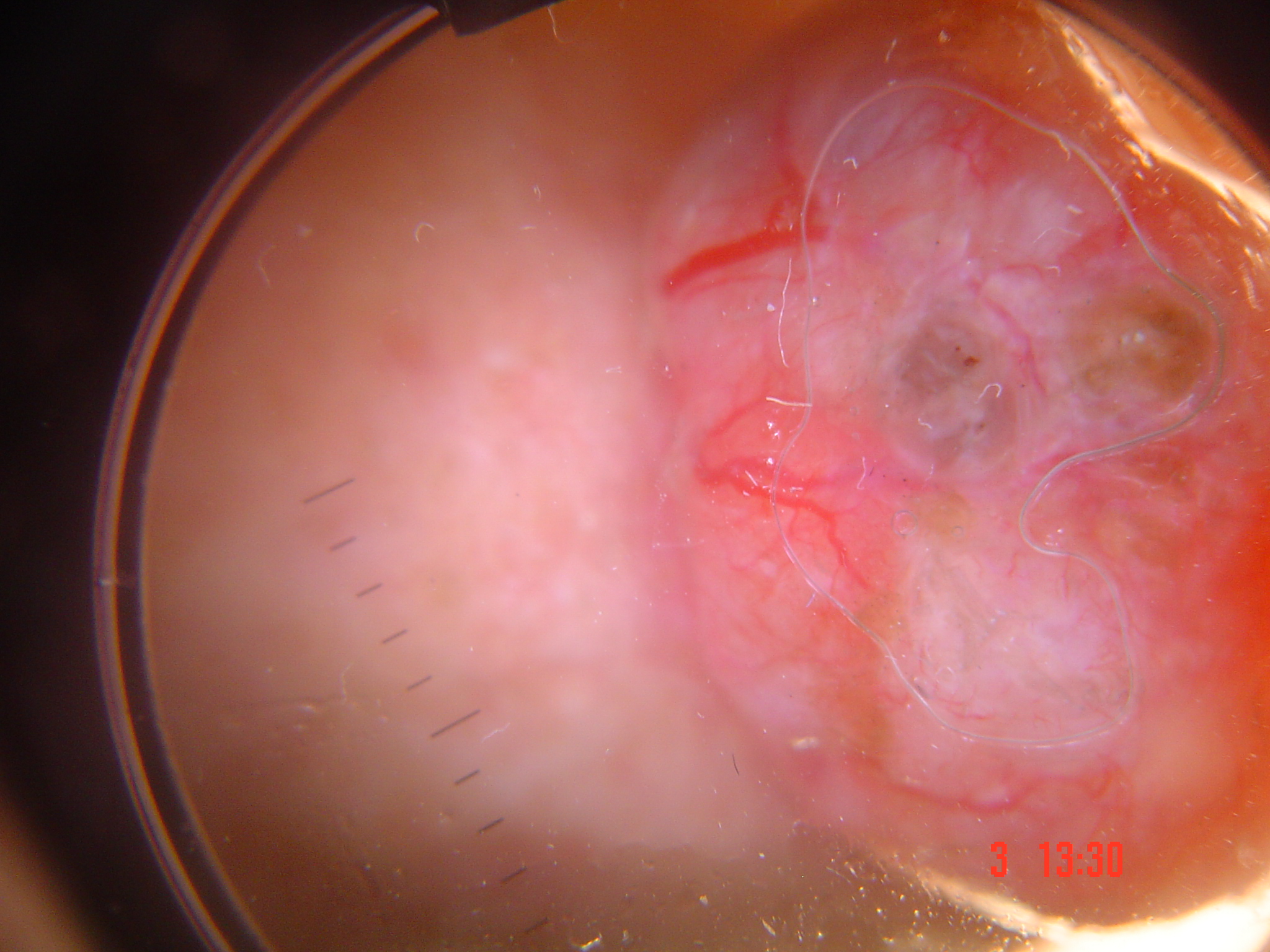Case: Dermoscopy of a skin lesion. Diagnosis: Confirmed on histopathology as a malignant, keratinocytic lesion — a basal cell carcinoma.